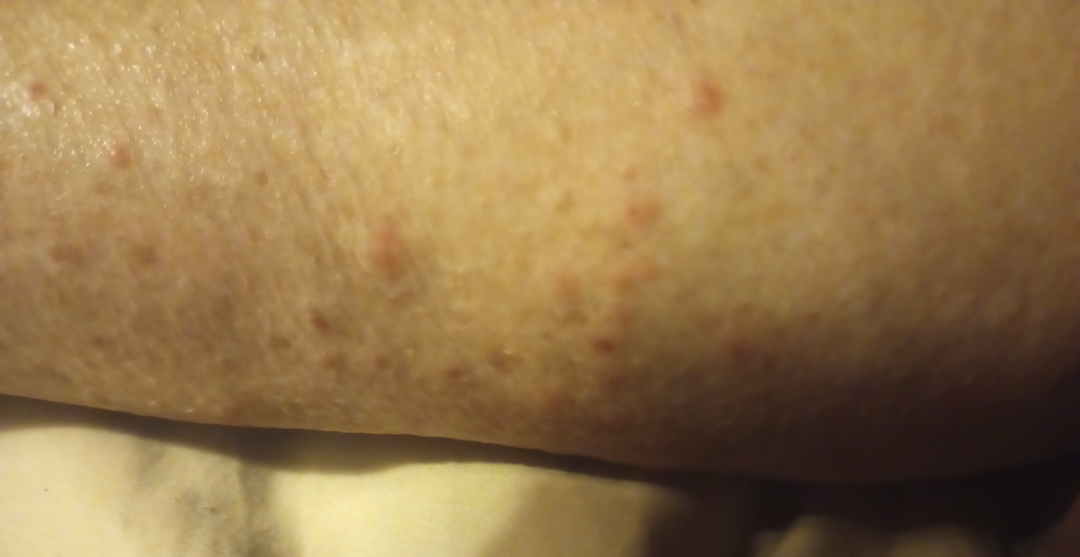{
  "assessment": "ungradable on photographic review",
  "shot_type": "at an angle"
}